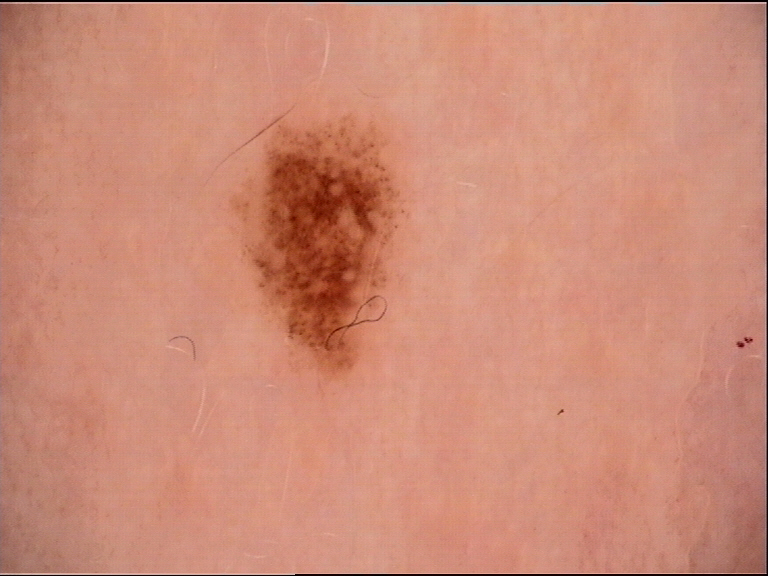modality: dermoscopy; diagnostic label: junctional nevus (expert consensus).